The contributor reports the condition has been present for less than one week · the contributor is a male aged 30–39 · this image was taken at an angle · texture is reported as raised or bumpy · the lesion is associated with itching.
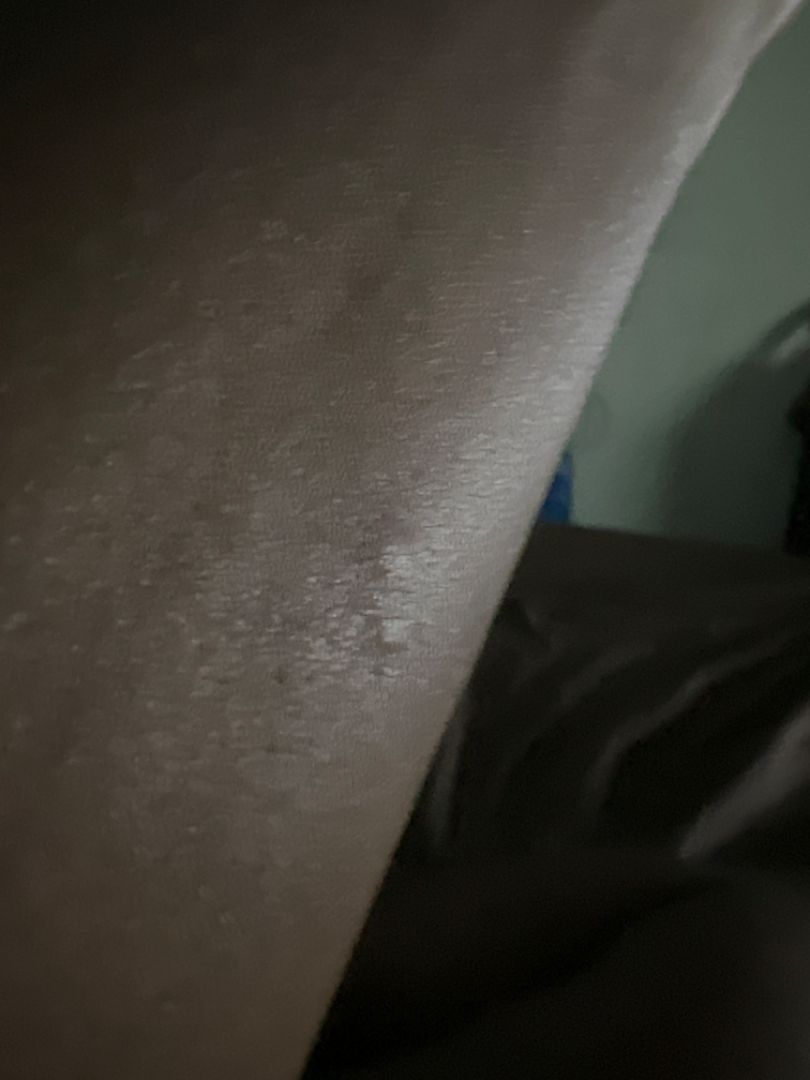On independent review by the dermatologists: most consistent with Insect Bite; also consider Allergic Contact Dermatitis.